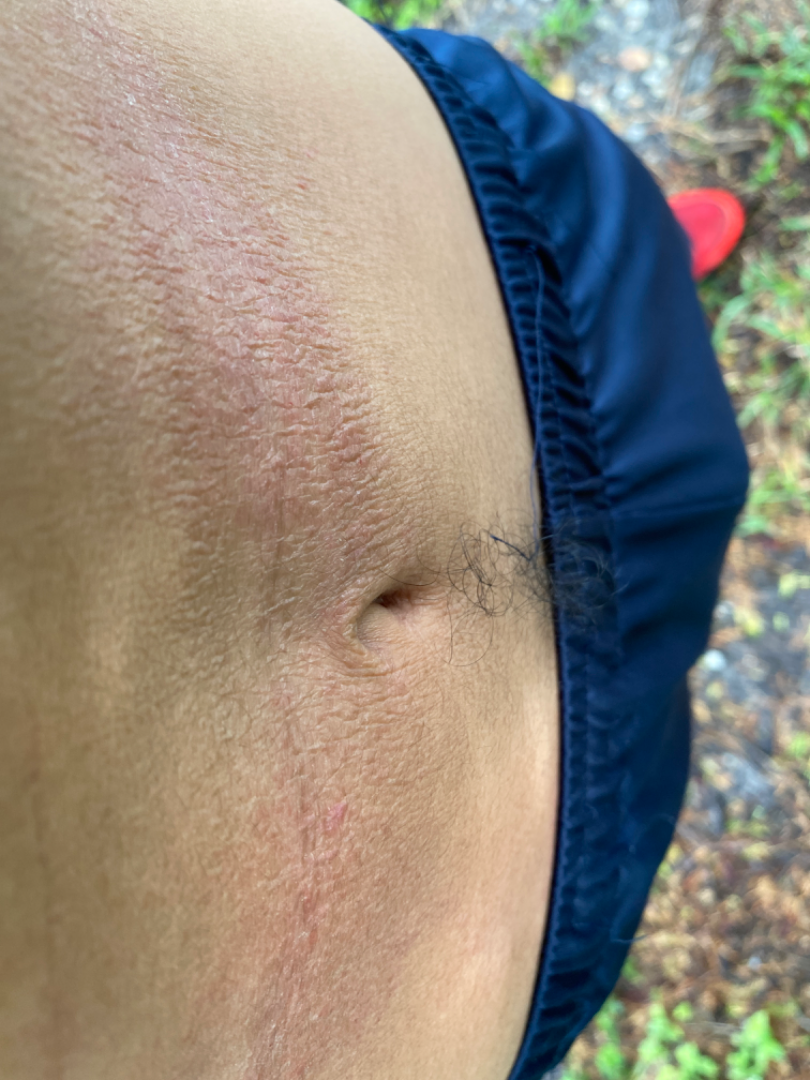{
  "differential": {
    "leading": [
      "Allergic Contact Dermatitis"
    ],
    "considered": [
      "Irritant Contact Dermatitis"
    ]
  }
}